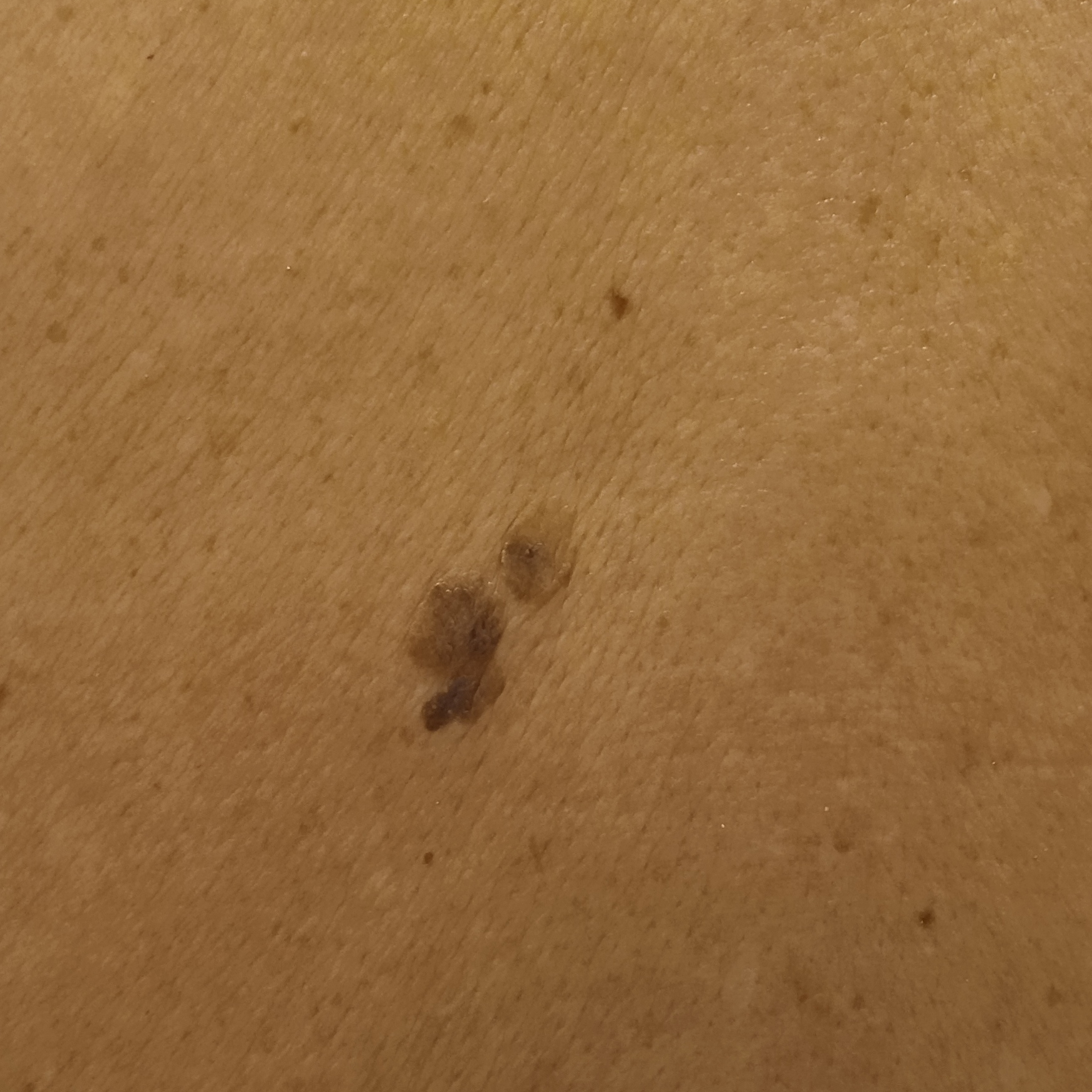Imaged for a research study, with no referral diagnosis recorded. The patient describes having a moderate number of moles. On a questionnaire the patient reported no sunbed use and no personal history of skin cancer. The patient says their skin tans without first burning. A male subject aged 72. A clinical photograph of a skin lesion. Located on the back. The lesion is about 12.8 mm across. The dermatologists' assessment was a seborrheic keratosis.